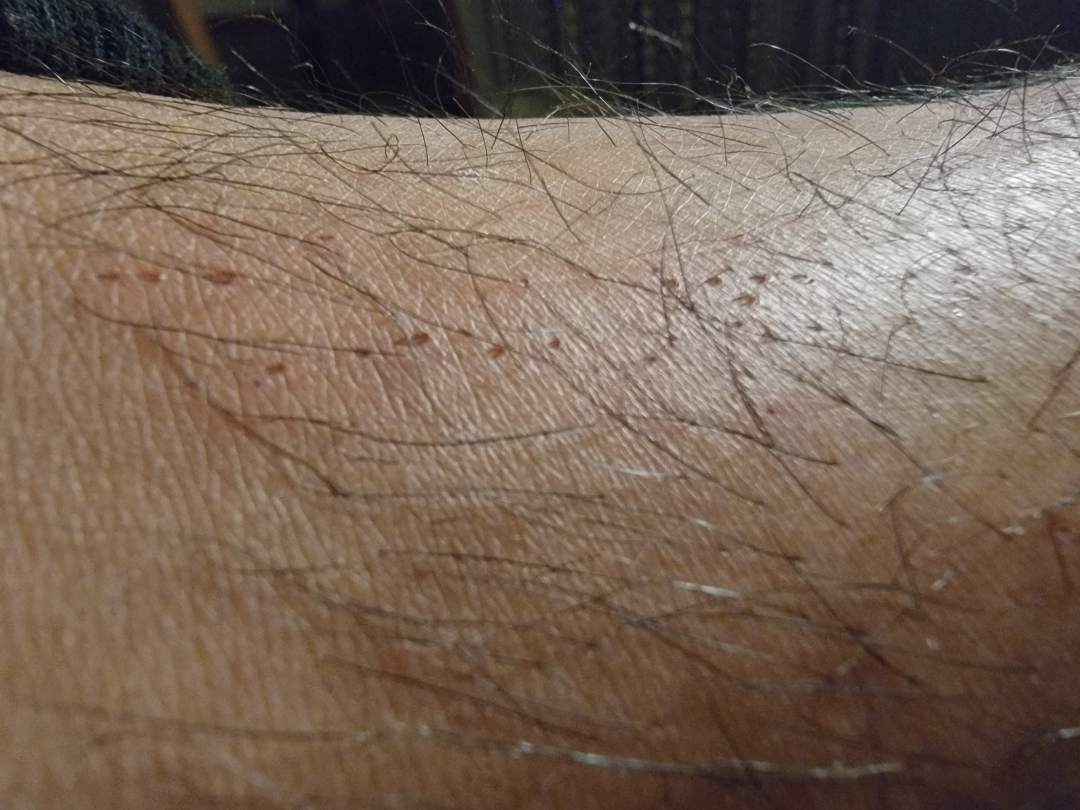assessment = not assessable; onset = less than one week; lesion symptoms = burning and bothersome appearance; self-categorized as = a rash; shot type = at an angle; contributor = male, age 18–29; location = leg.